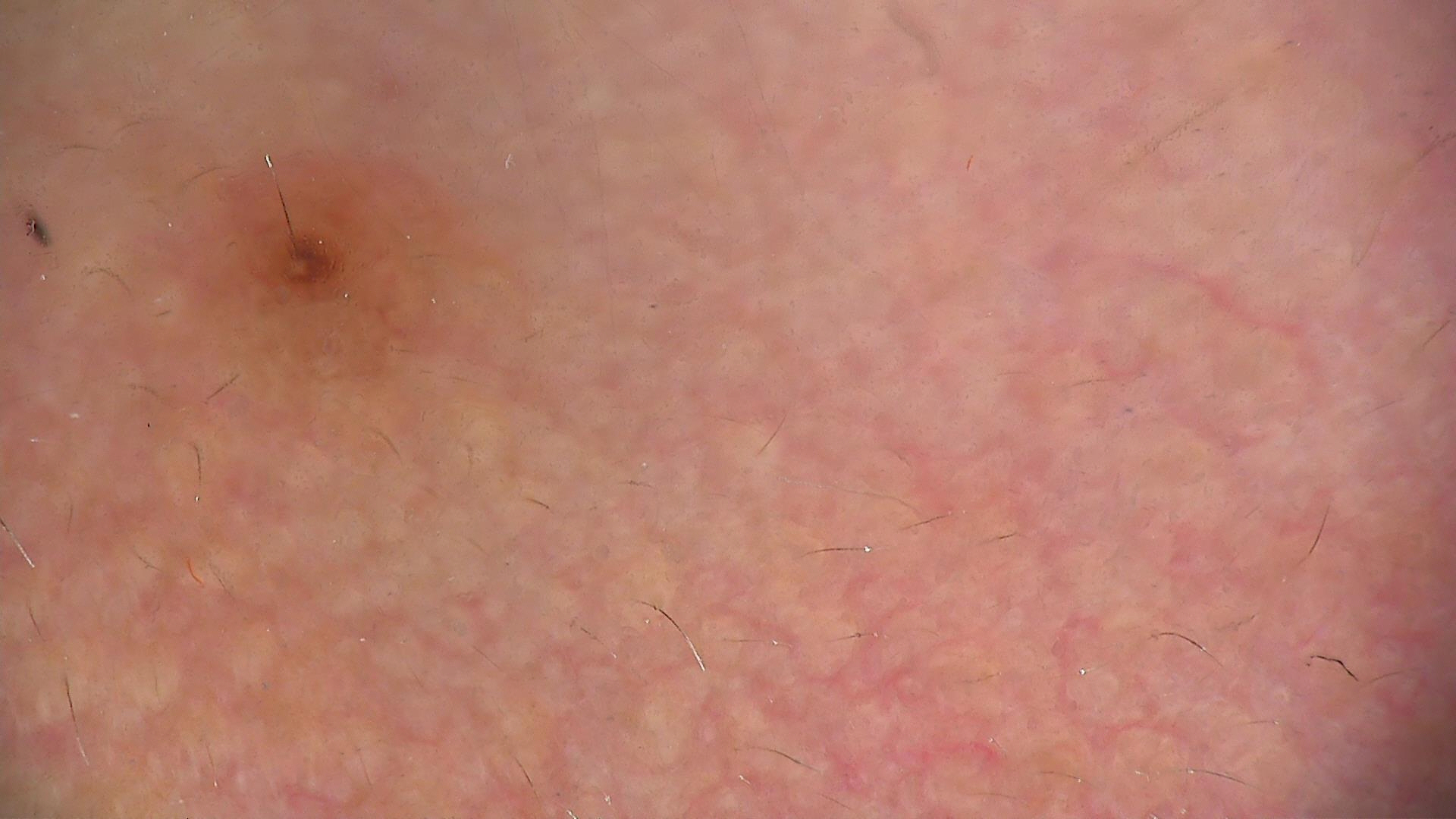Findings:
A dermoscopic photograph of a skin lesion.
Conclusion:
The diagnostic label was a banal lesion — a junctional nevus.